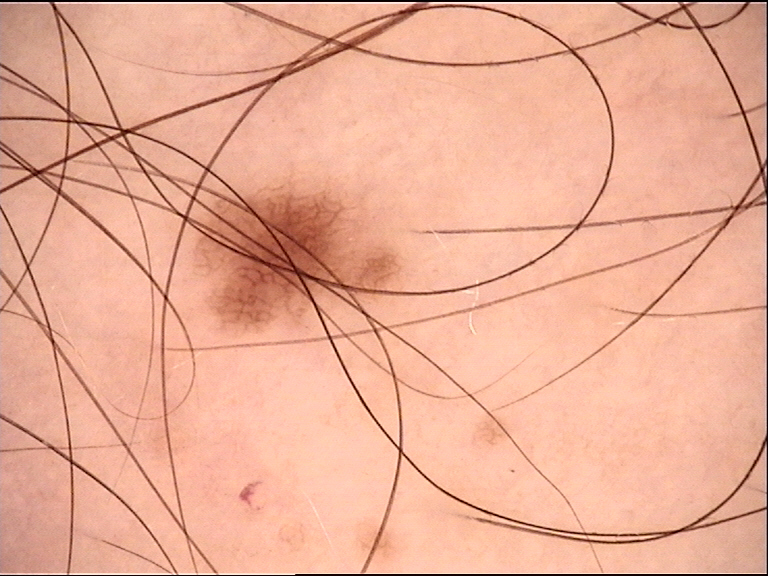Classified as a dysplastic junctional nevus.